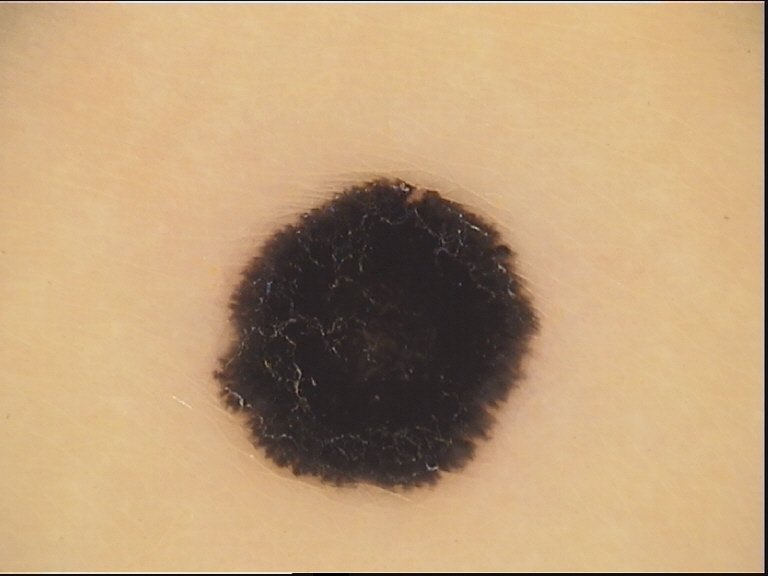modality = dermatoscopy | category = junctional, dysplastic | label = Spitz/Reed nevus (expert consensus).